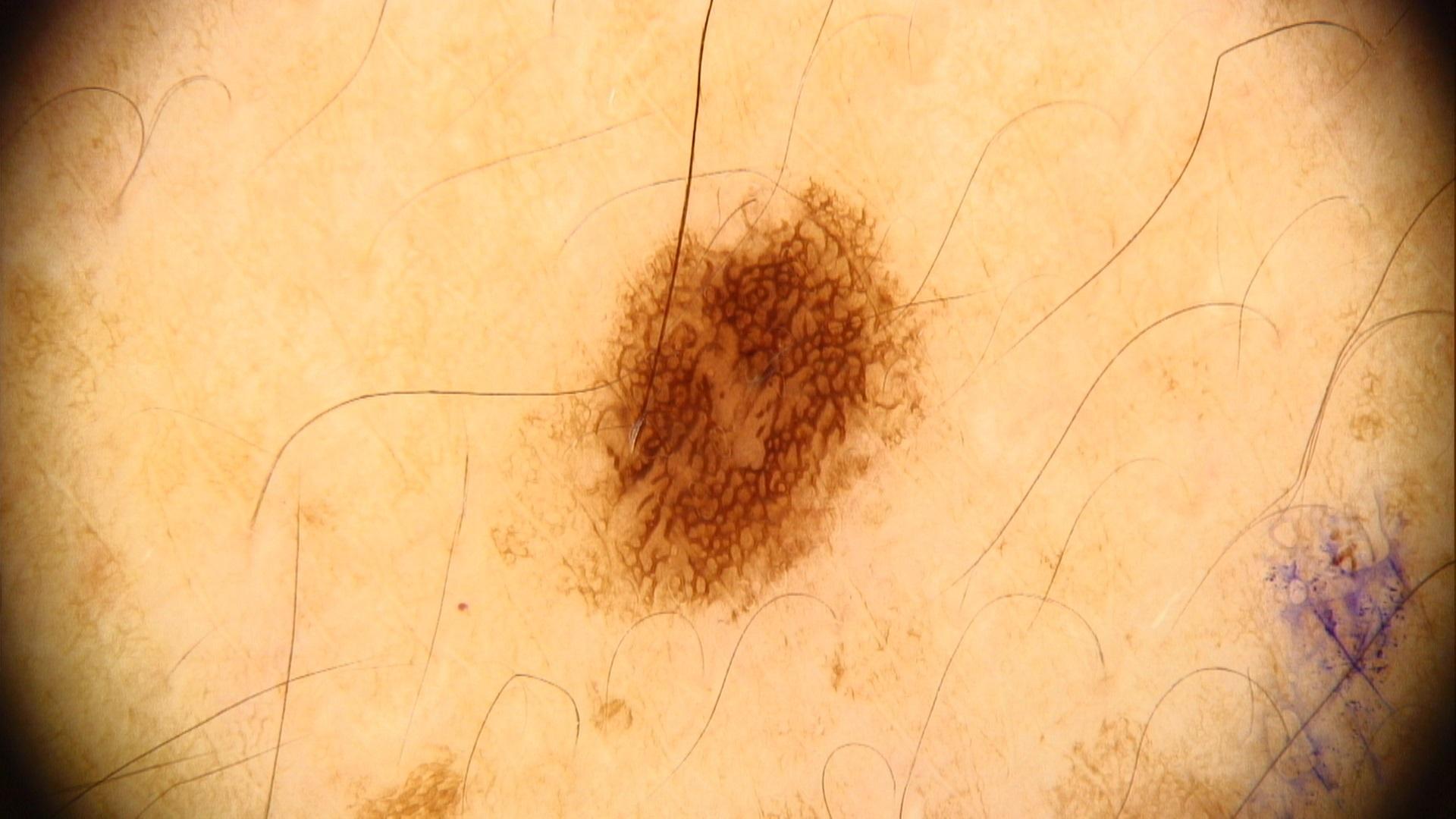A dermoscopy image of a single skin lesion. A male patient aged 58-62. Located on the trunk. The clinical impression was a benign lesion — a nevus.